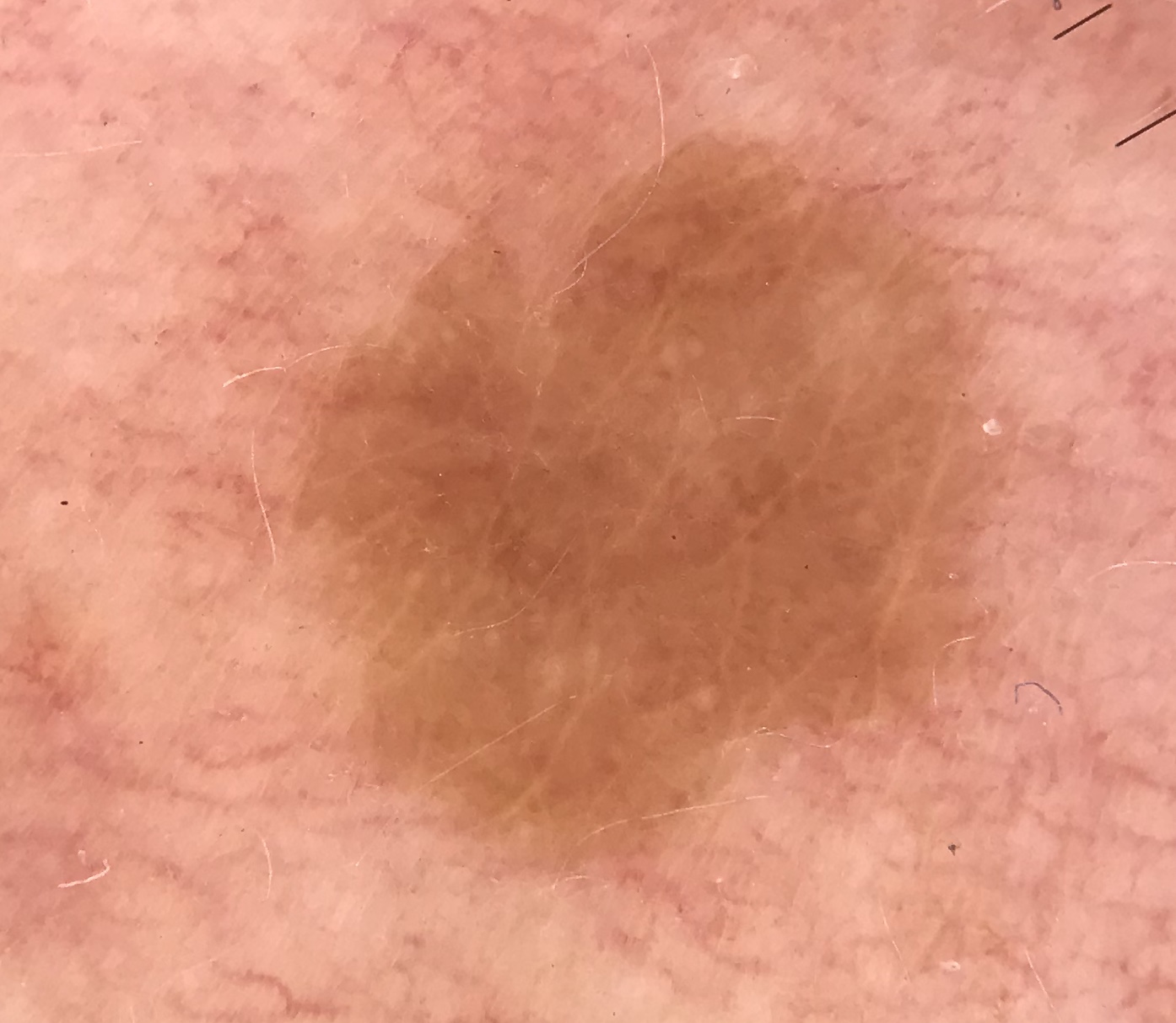subtype=keratinocytic | diagnosis=seborrheic keratosis (expert consensus).